A female subject aged 48; the patient says their skin reddens painfully with sun exposure; few moles overall by the patient's own estimate — 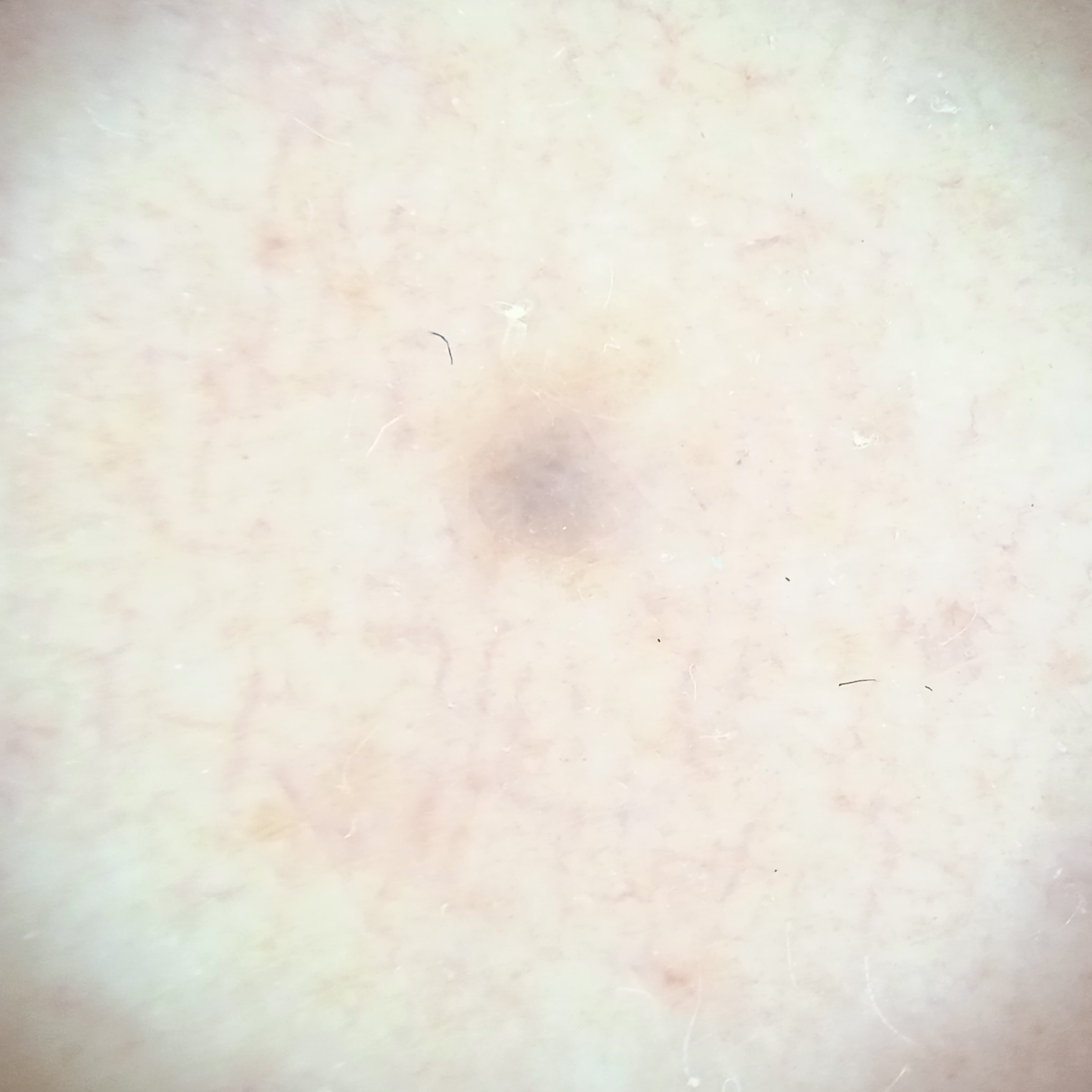body site = an arm
size = 1.8 mm
assessment = melanocytic nevus (dermatologist consensus)